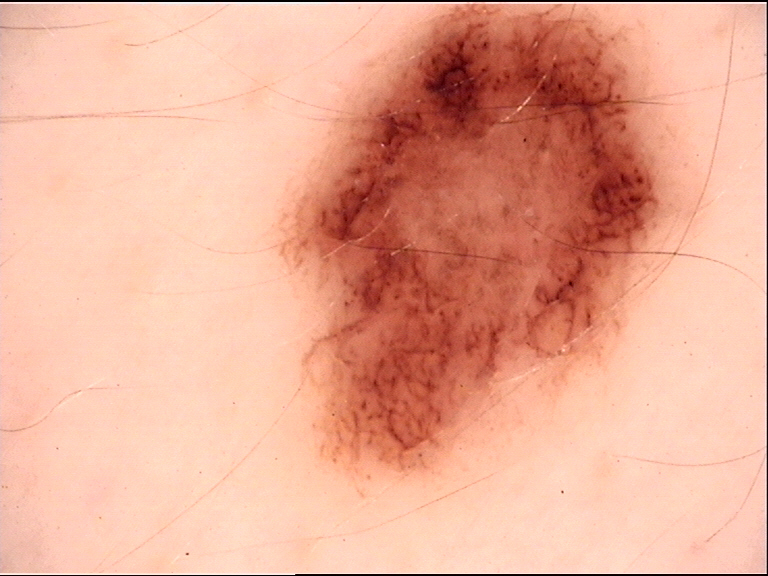Conclusion:
Classified as a dysplastic junctional nevus.